A male patient, roughly 50 years of age; dermoscopy of a skin lesion.
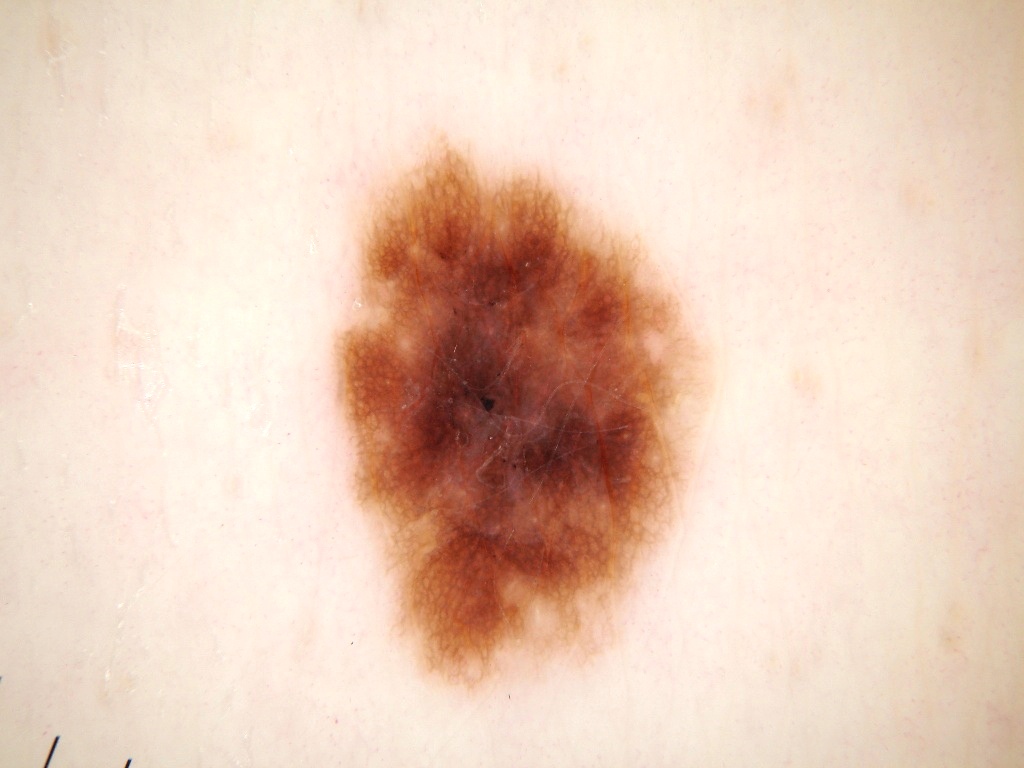The visible lesion spans left=323, top=132, right=709, bottom=704. Dermoscopic examination shows milia-like cysts and pigment network, with no globules, negative network, or streaks. Diagnosed as a melanocytic nevus.